Dermoscopy of a skin lesion:
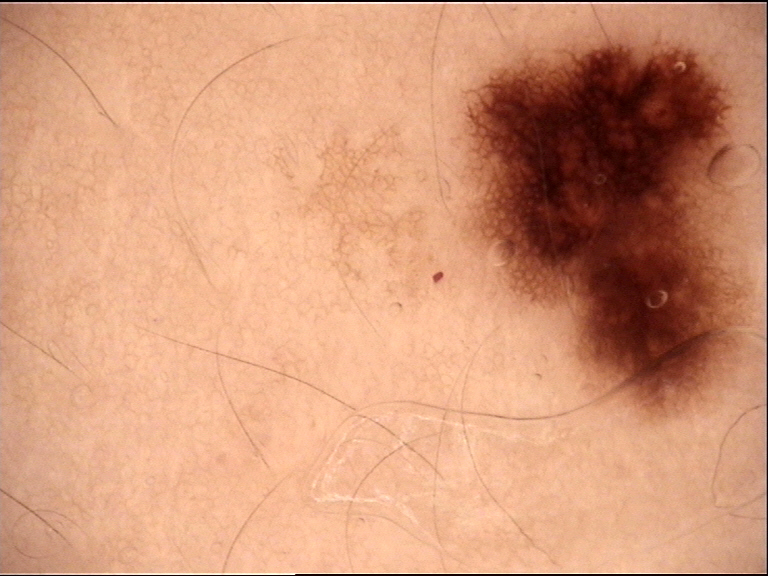| key | value |
|---|---|
| label | dysplastic junctional nevus (expert consensus) |